A dermoscopic close-up of a skin lesion:
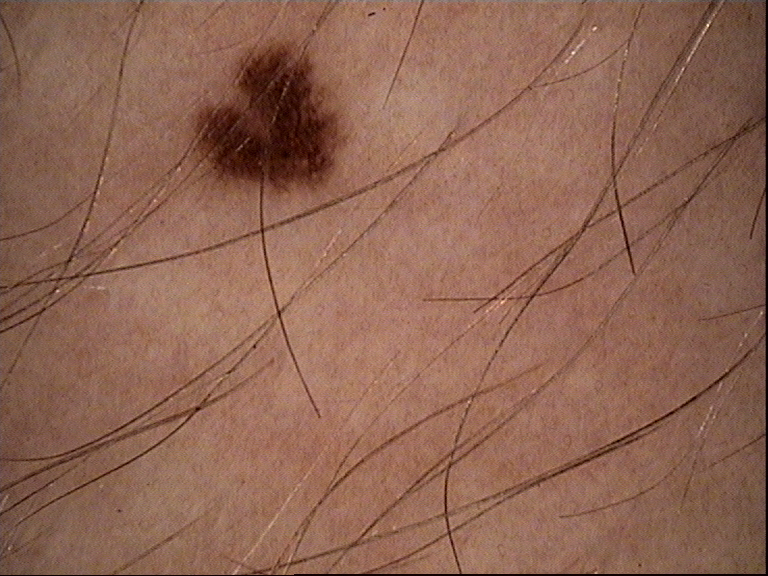Impression:
The diagnosis was a dysplastic junctional nevus.